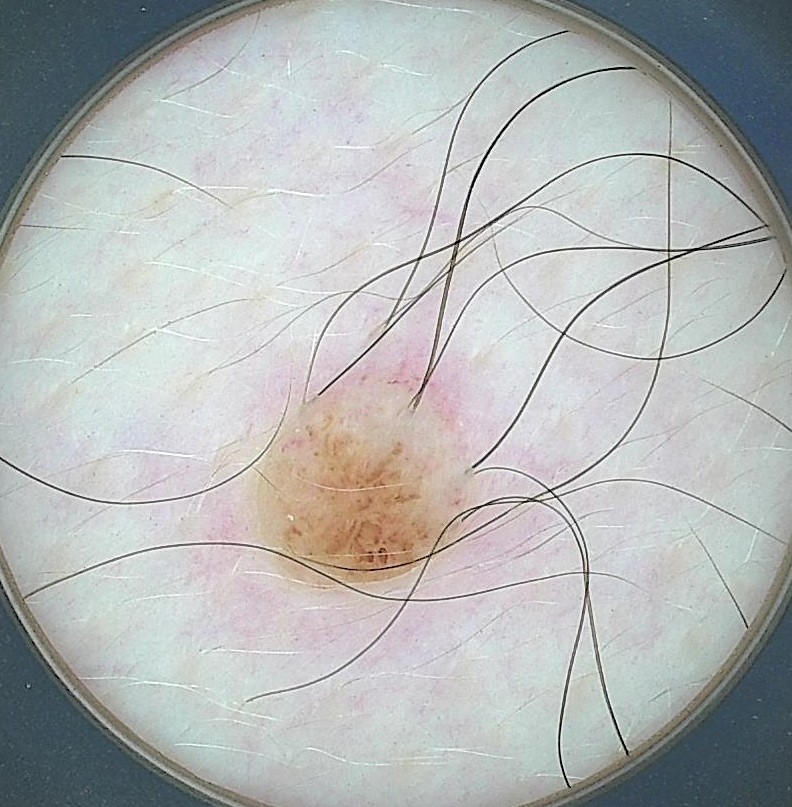Impression: Classified as a dermal nevus.